The patient is a female aged 18–29; close-up view; the front of the torso is involved: 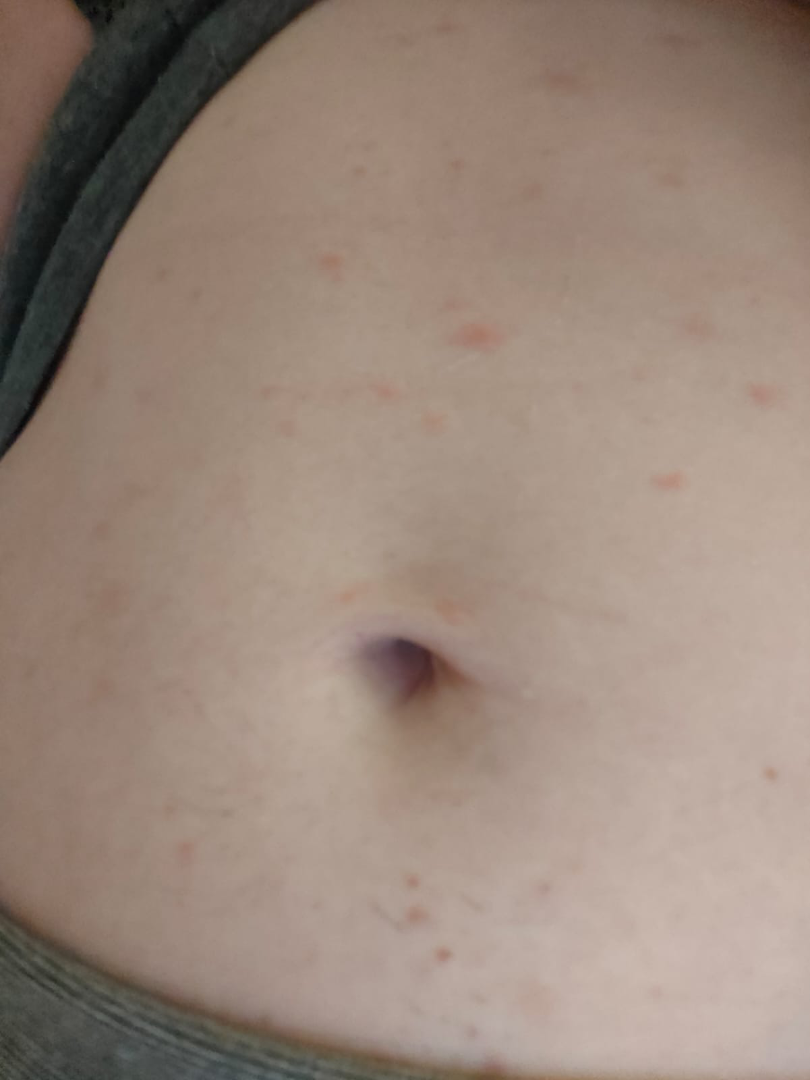Q: Could the case be diagnosed?
A: could not be assessed